Reported lesion symptoms include bothersome appearance, itching and darkening; the lesion is described as rough or flaky; the lesion involves the arm and top or side of the foot; the patient considered this a rash; the patient also reports fatigue; the photograph was taken at an angle; the patient notes the condition has been present for three to twelve months; skin tone: Fitzpatrick phototype V: 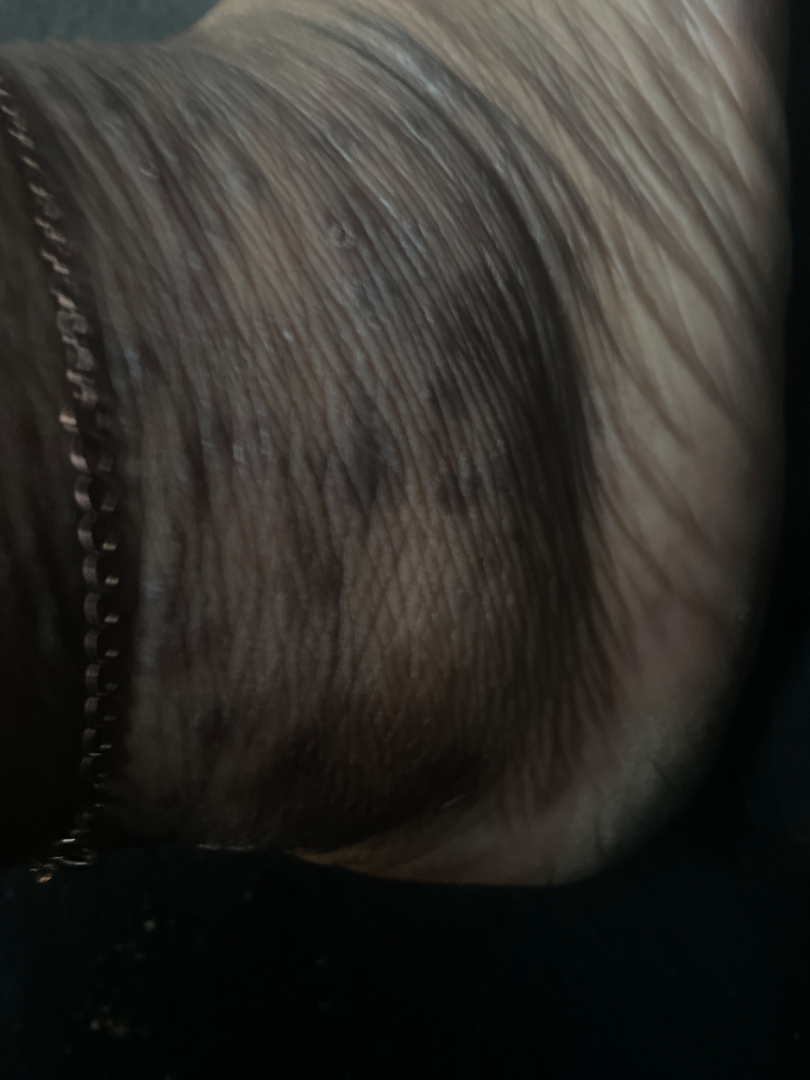Notes:
* differential · the leading consideration is Lichen planus/lichenoid eruption; possibly Chronic dermatitis, NOS; also consider Drug Rash